A dermoscopy image of a single skin lesion.
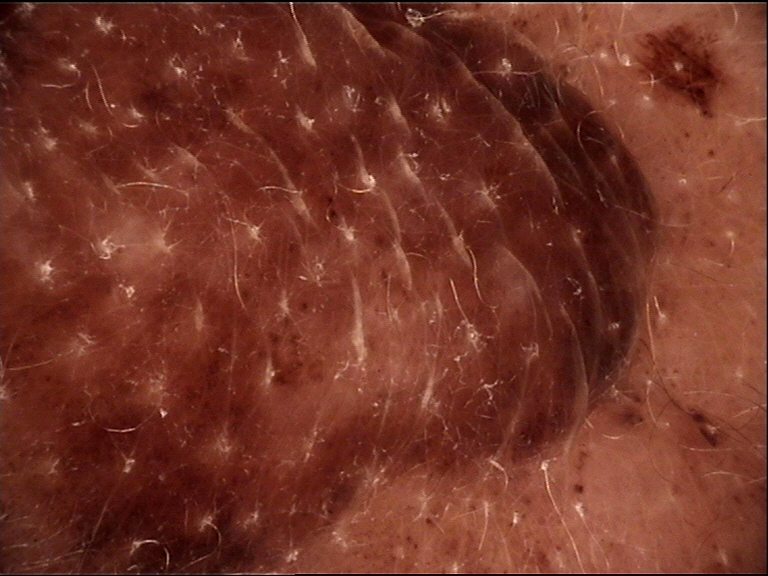The morphology is that of a banal lesion. The diagnosis was a congenital compound nevus.